A male subject 62 years old; collected as part of a research study, without a referral diagnosis; few moles overall by the patient's own estimate; by self-report, no family history of skin cancer and no personal history of cancer; a clinical photograph showing a skin lesion; the patient says their skin reddens with sun exposure:
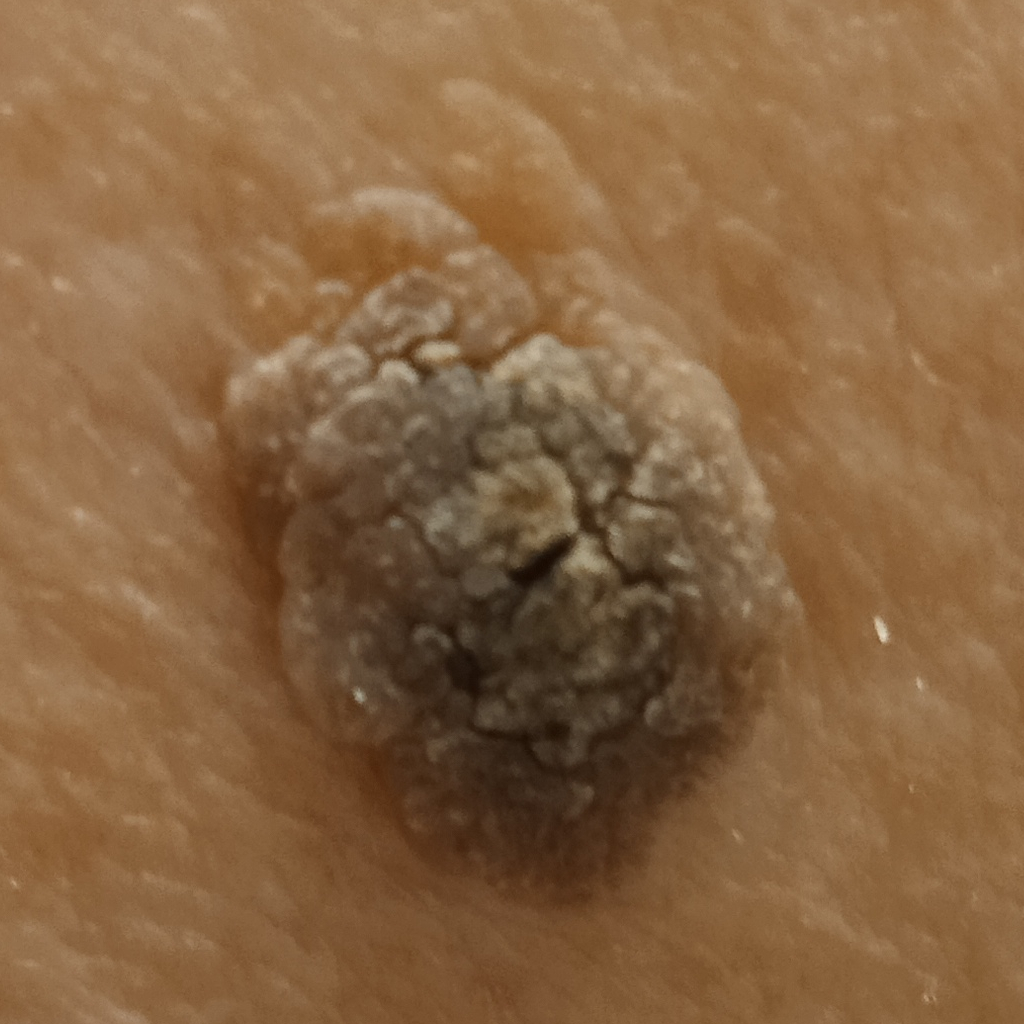Located on the back.
The lesion measures approximately 10.9 mm.
The diagnostic impression was a seborrheic keratosis.